A dermatoscopic image of a skin lesion:
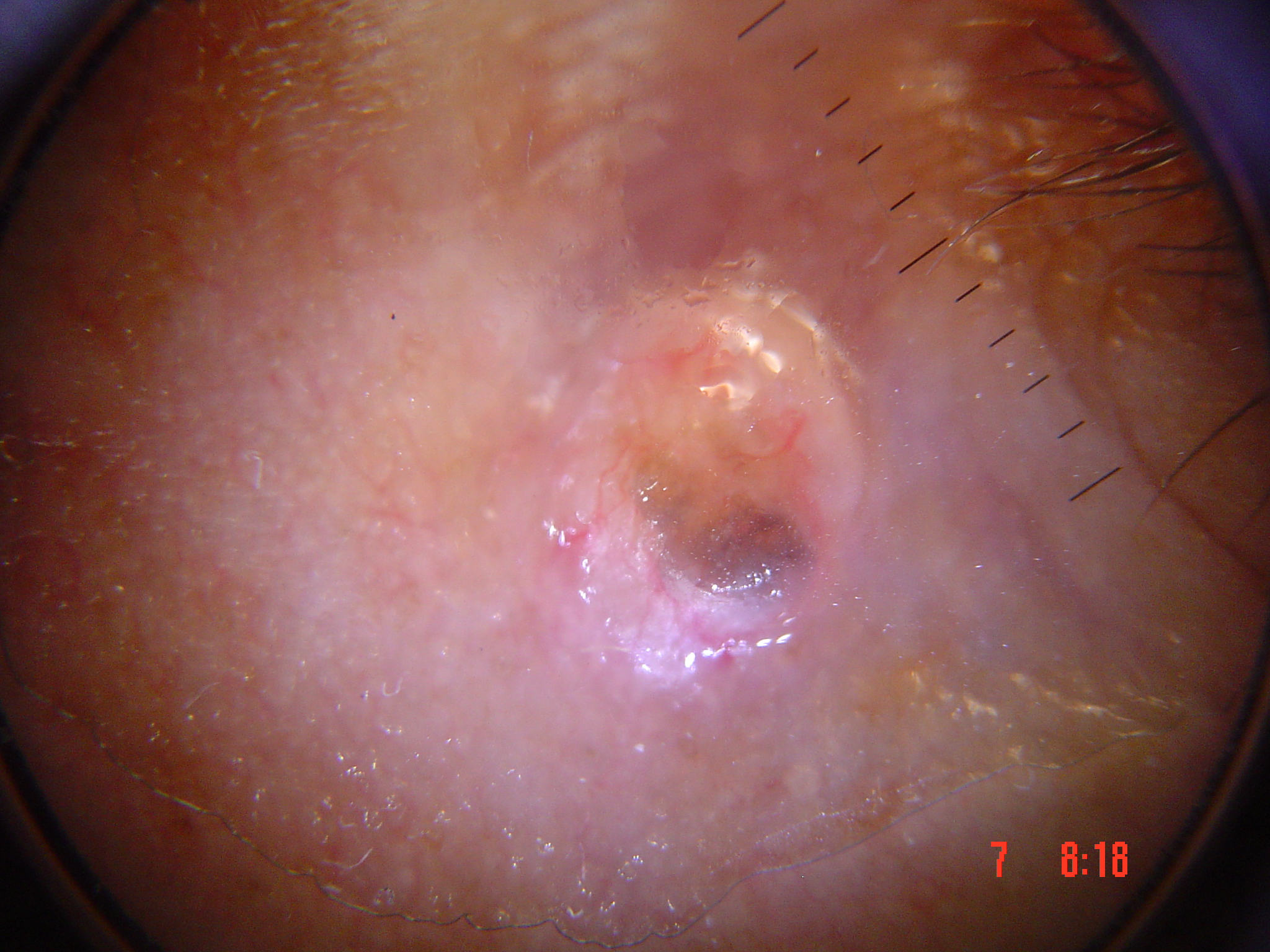lesion type=keratinocytic
class=basal cell carcinoma (biopsy-proven)